A dermoscopic photograph of a skin lesion.
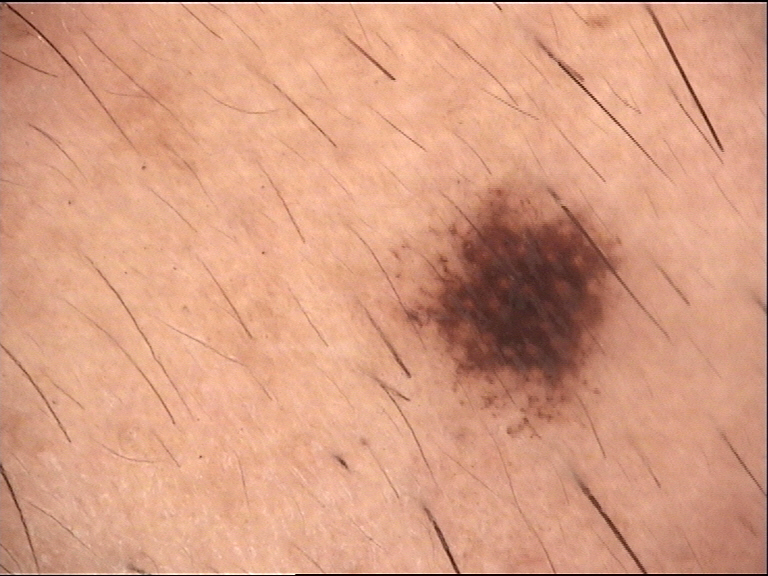The architecture is that of a banal lesion.
Classified as a compound nevus.